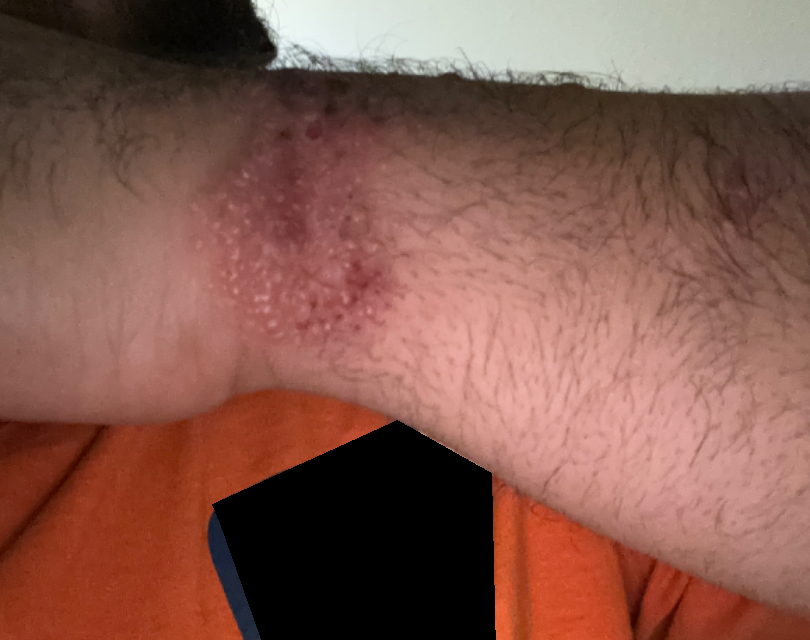The reviewing clinician's impression was: Allergic Contact Dermatitis (leading); Irritant Contact Dermatitis (considered).